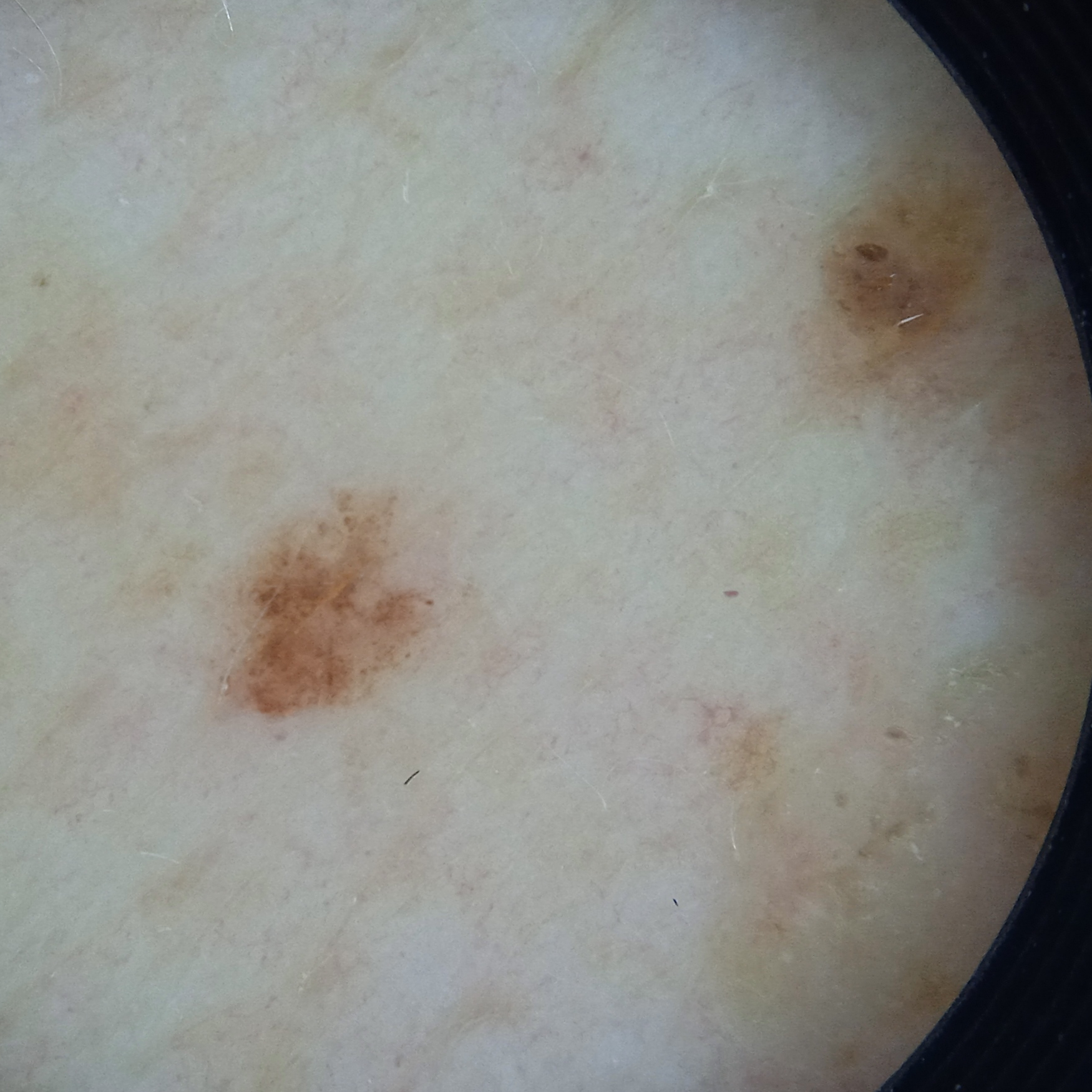Case summary: A dermatoscopic image of a skin lesion. The patient describes having few moles overall. The patient says their skin reddens with sun exposure. A male subject age 78. Collected as part of a research study, without a referral diagnosis. The lesion involves the back. The lesion measures approximately 3.1 mm. Impression: The lesion was assessed as a seborrheic keratosis.